Human graders estimated 2 on the Monk Skin Tone · the photograph was taken at an angle · the lesion is described as raised or bumpy · the affected area is the arm · reported lesion symptoms include itching: 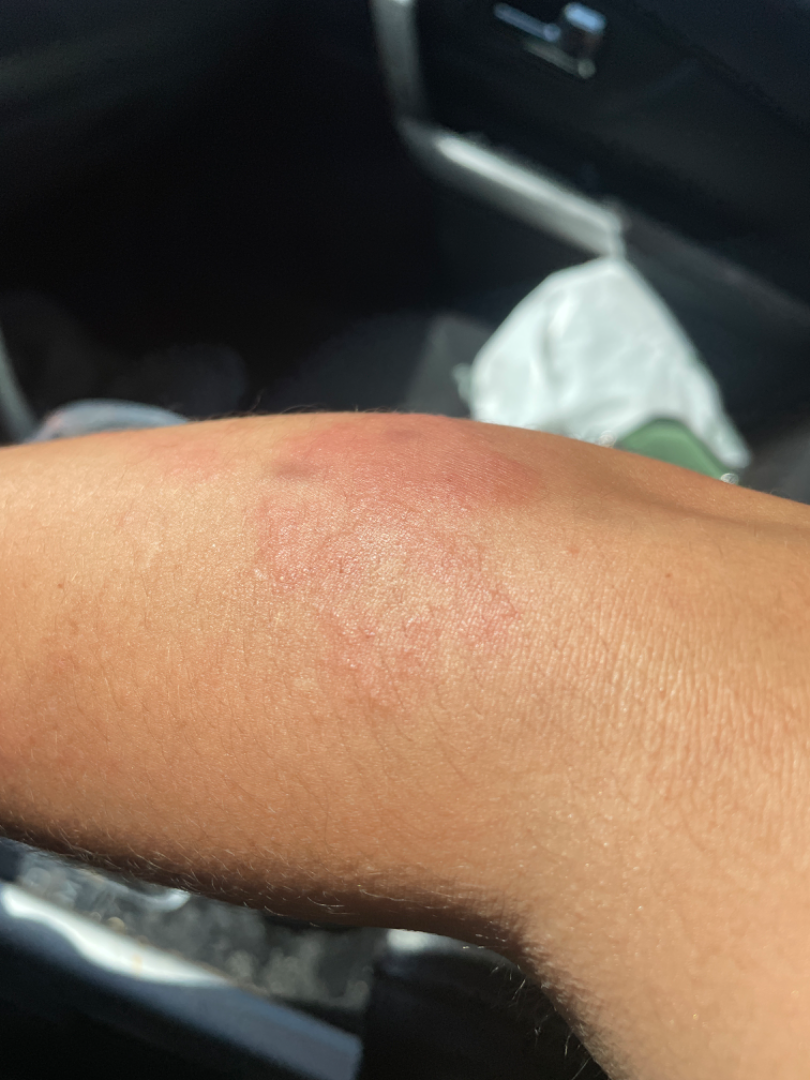| key | value |
|---|---|
| differential diagnosis | most likely Allergic Contact Dermatitis; with consideration of Herpes Simplex; less probable is Herpes Zoster |